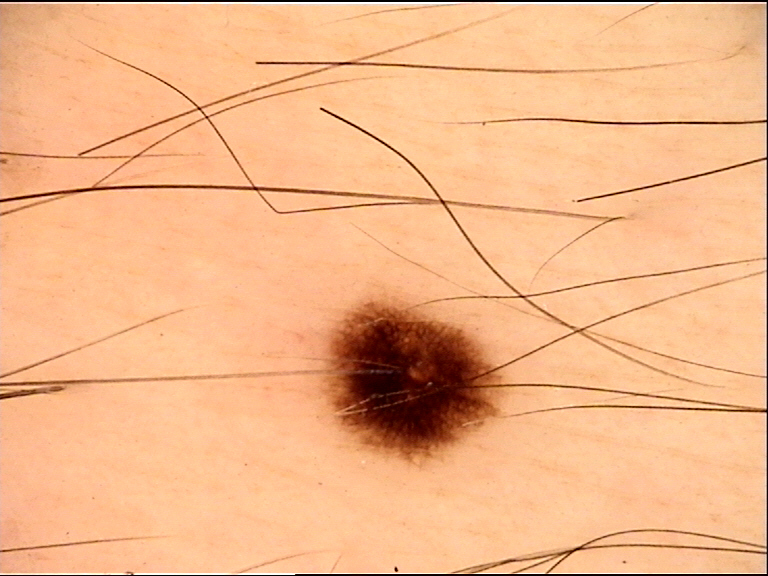The diagnostic label was a junctional nevus.